Acquired for a research image collection, with no referral diagnosis; a male patient aged 72; a dermoscopy image of a skin lesion:
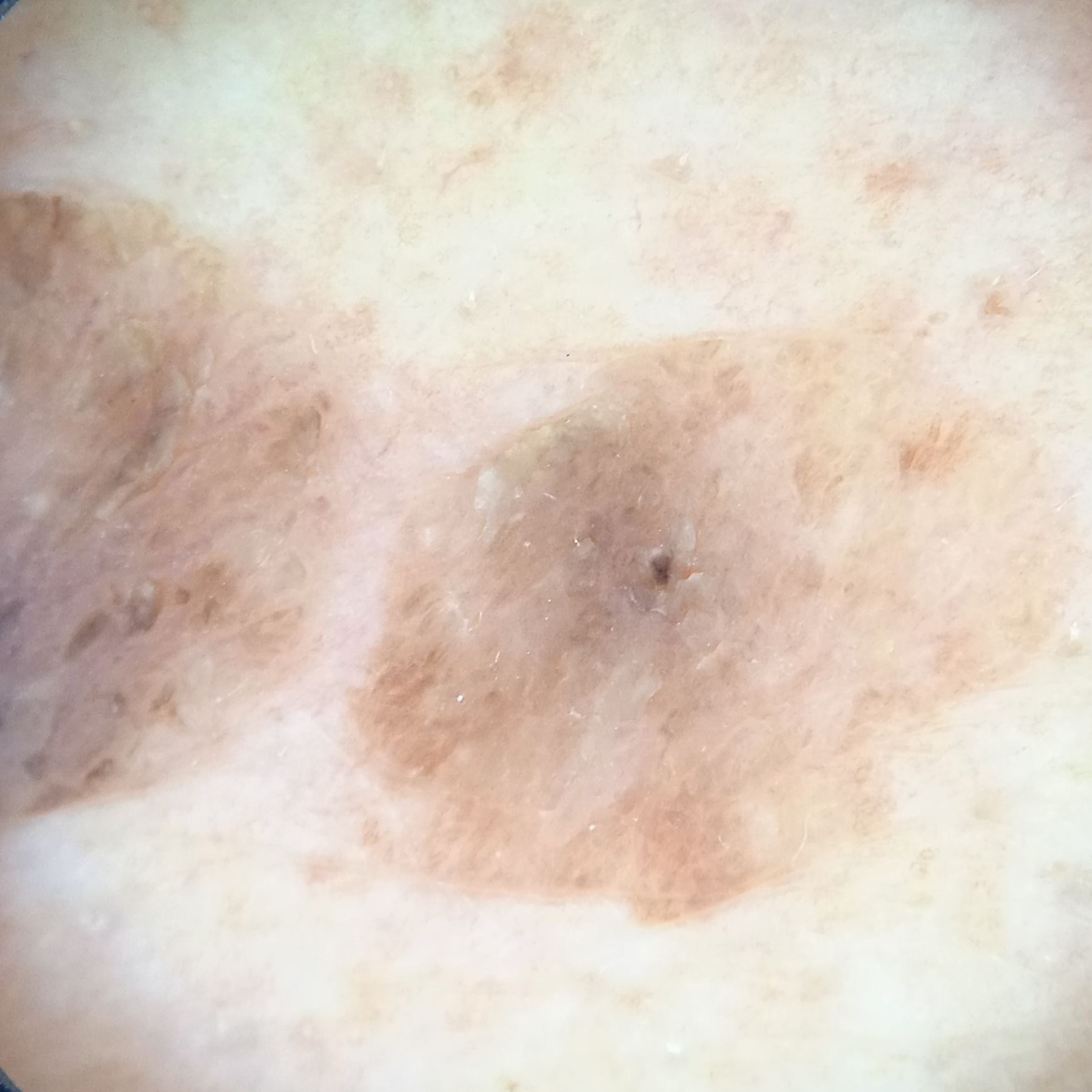The lesion involves the back.
The lesion is about 12.8 mm across.
The diagnostic impression was a seborrheic keratosis.